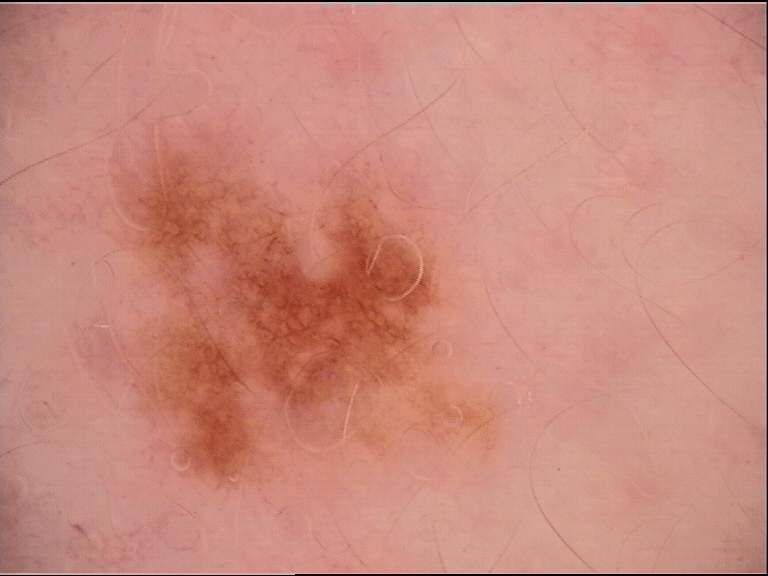<case>
  <image>dermoscopy</image>
  <diagnosis>
    <name>dysplastic junctional nevus</name>
    <code>jd</code>
    <malignancy>benign</malignancy>
    <super_class>melanocytic</super_class>
    <confirmation>expert consensus</confirmation>
  </diagnosis>
</case>